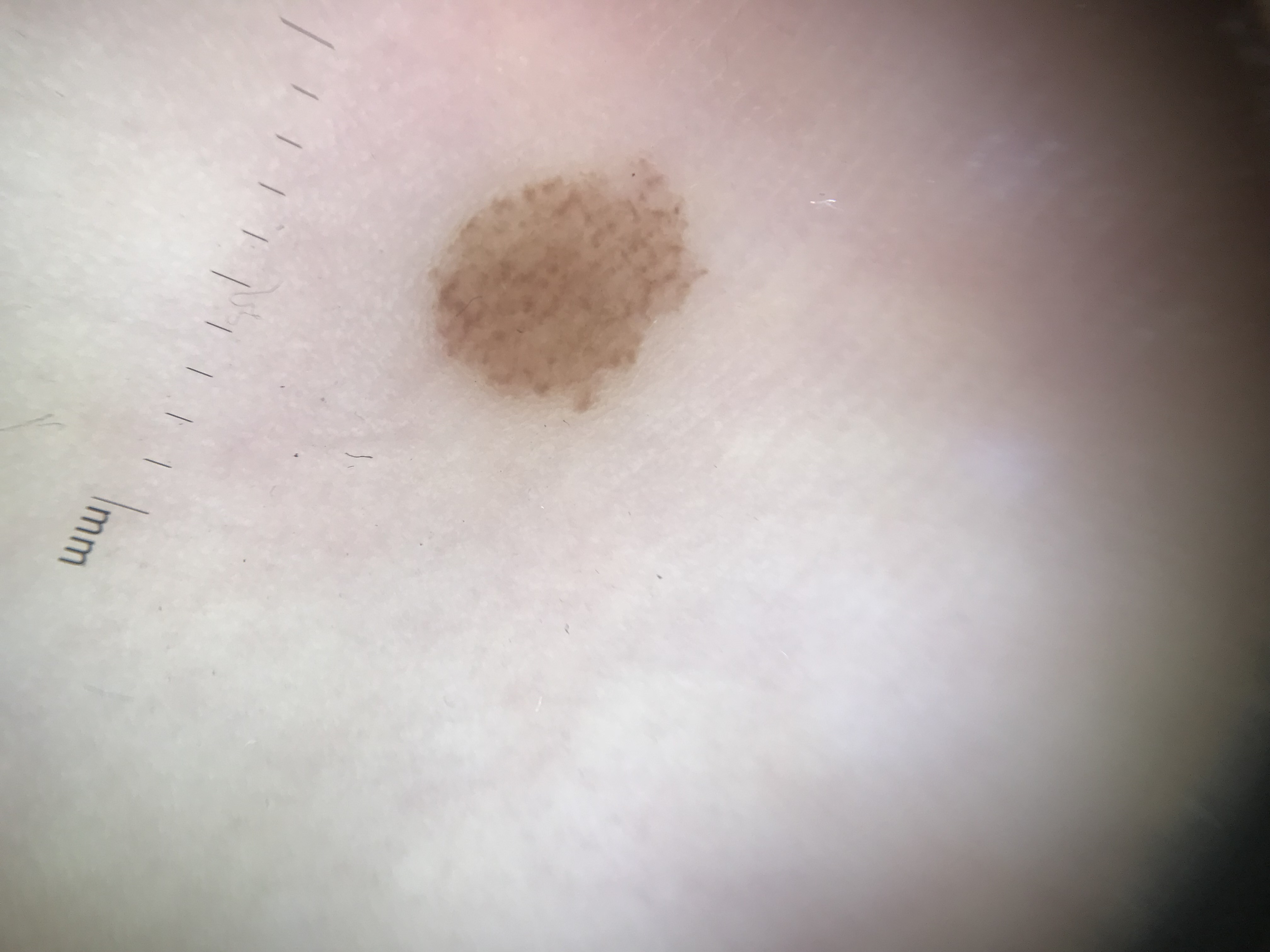diagnosis:
  name: acral dysplastic junctional nevus
  code: ajd
  malignancy: benign
  super_class: melanocytic
  confirmation: expert consensus